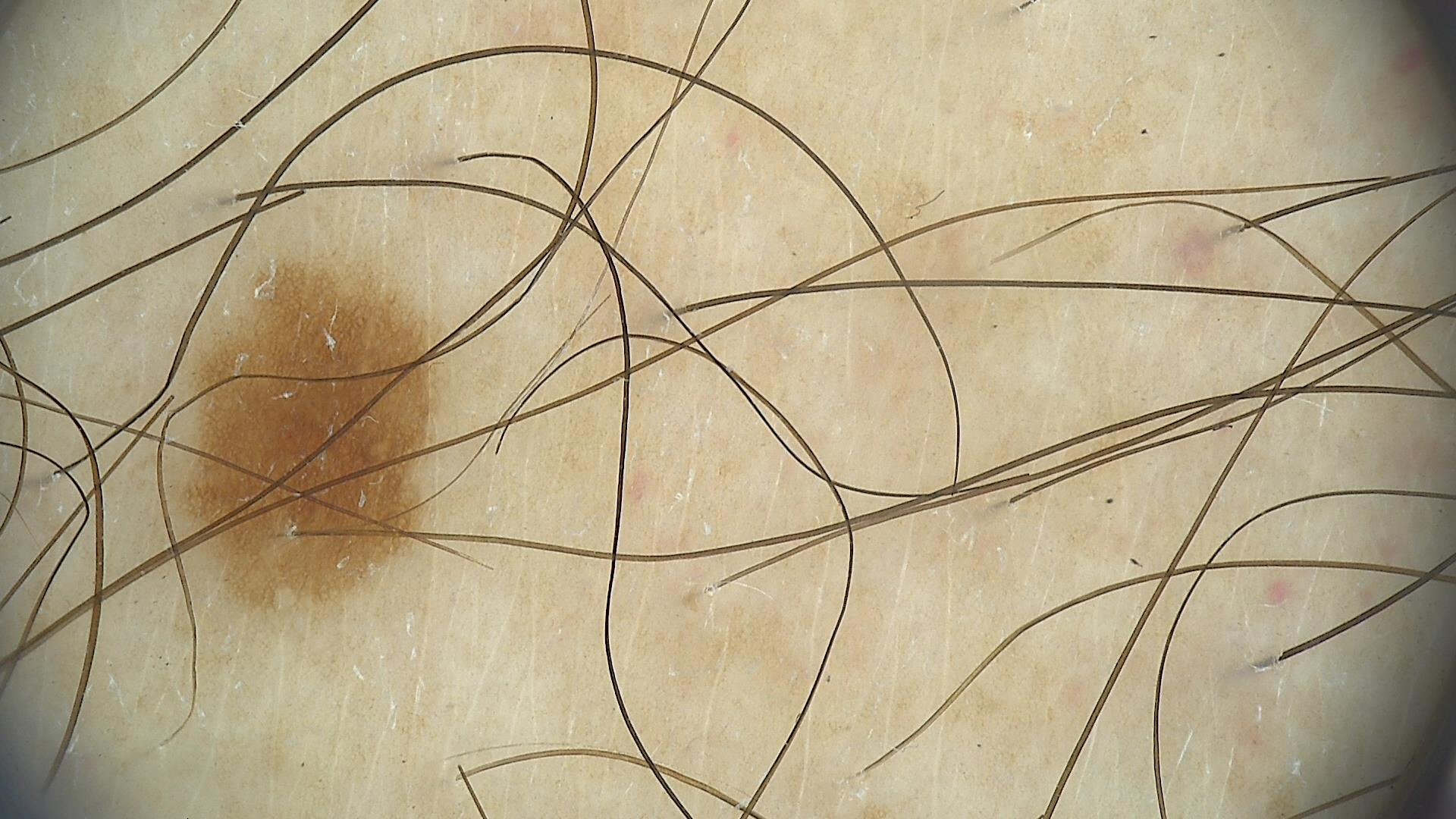diagnosis:
  name: dysplastic junctional nevus
  code: jd
  malignancy: benign
  super_class: melanocytic
  confirmation: expert consensus